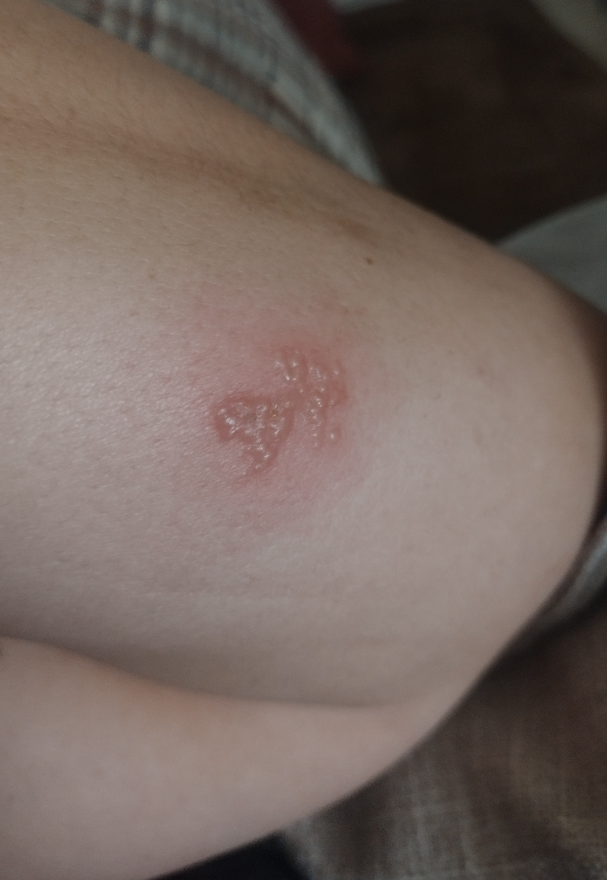Patient information:
This is a close-up image. The affected area is the arm.
Review:
On remote dermatologist review, the differential includes Allergic Contact Dermatitis and Herpes Simplex, with no clear leading consideration.